A skin lesion imaged with a dermatoscope: 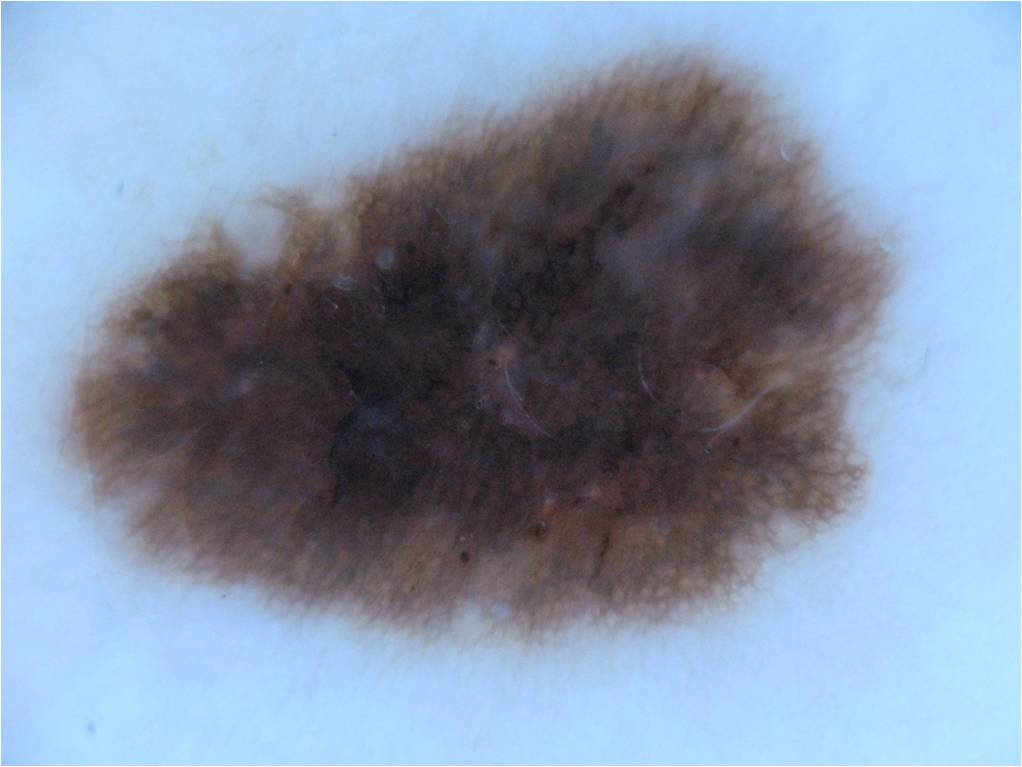lesion_location:
  bbox_xyxy:
    - 51
    - 47
    - 898
    - 634
diagnosis:
  name: melanocytic nevus
  malignancy: benign
  lineage: melanocytic
  provenance: clinical